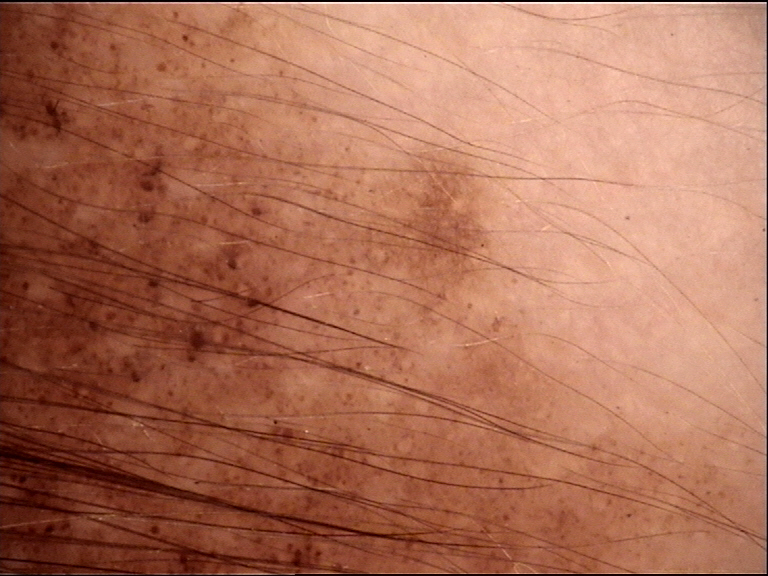The diagnosis was a congenital junctional nevus.